The subject is a female aged 70–79; reported duration is less than one week; the patient reports itching and bothersome appearance; the patient reported no systemic symptoms; the affected area is the leg and top or side of the foot; a close-up photograph; the lesion is described as flat and raised or bumpy — 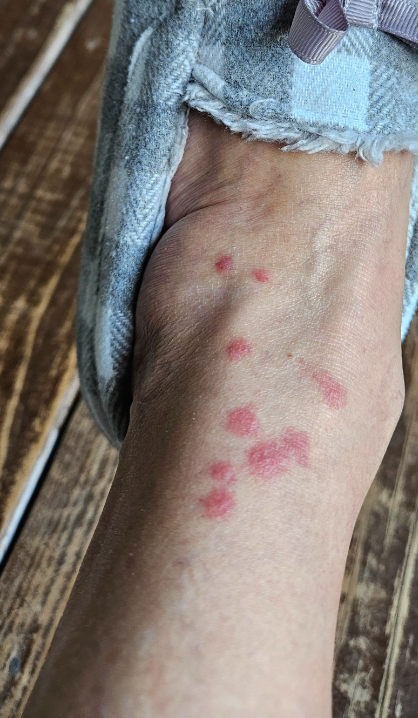dermatologist impression: Insect Bite (0.41); Dermatosis due to flea (0.41); Vasculitis of the skin (0.18).